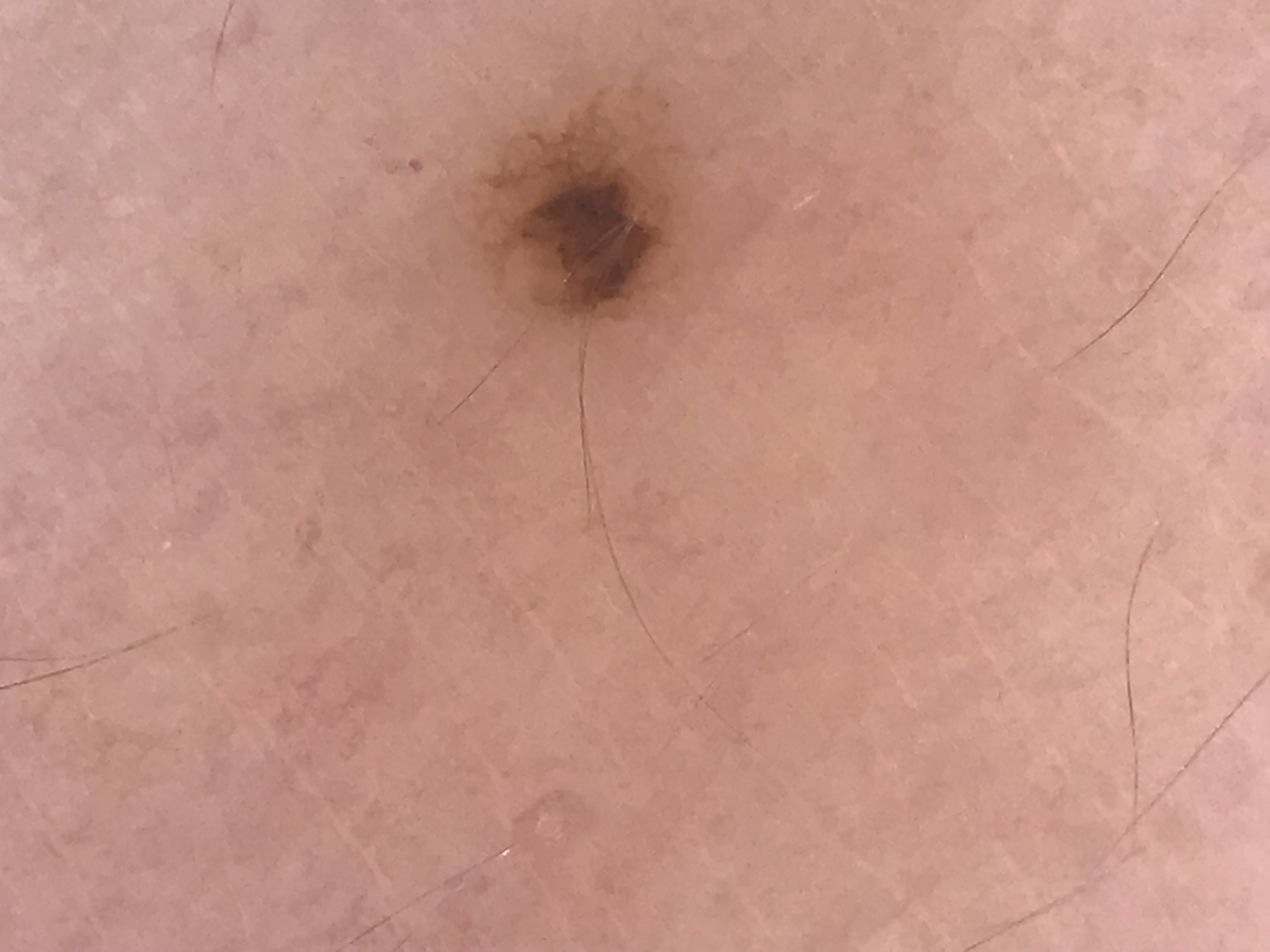A dermoscopy image of a single skin lesion. Classified as a banal lesion — a junctional nevus.